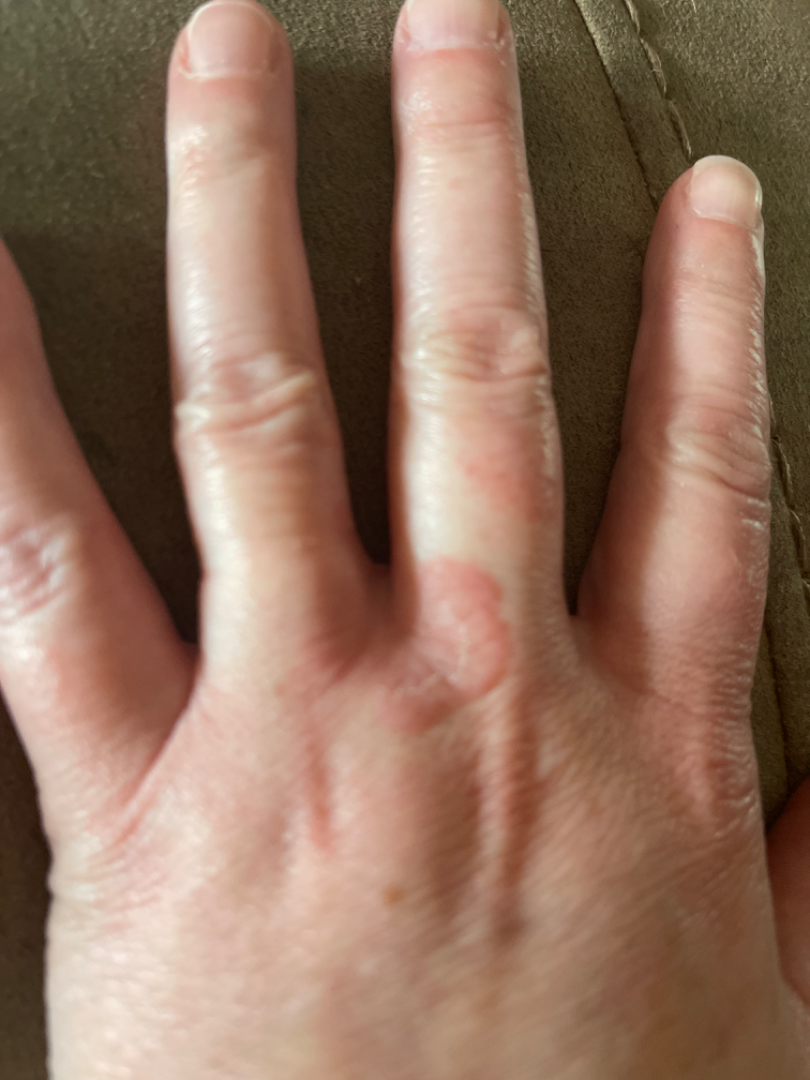In keeping with Granuloma annulare.